The photograph is a close-up of the affected area:
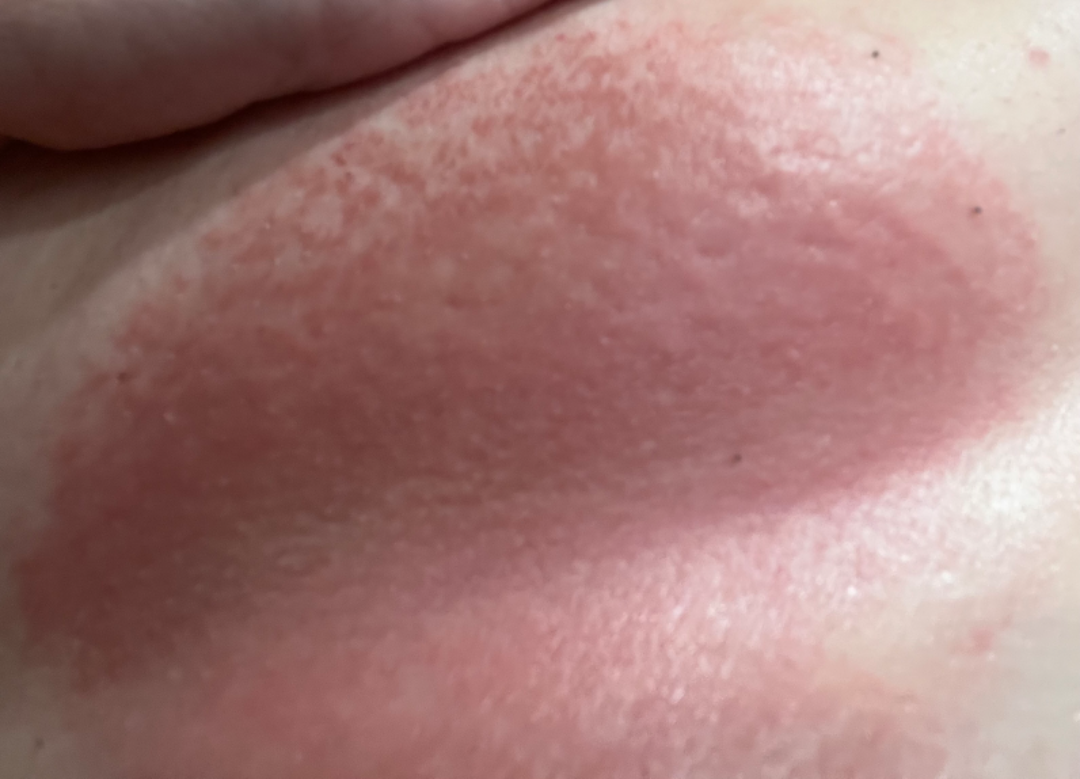Patient information: Fitzpatrick phototype II; non-clinician graders estimated a Monk Skin Tone of 2. The contributor reports burning, itching and pain. The patient described the issue as a rash. Review: The reviewing dermatologist's impression was: Allergic Contact Dermatitis (most likely); Eczema (considered); Cellulitis (considered).